The photograph is a close-up of the affected area · the affected area is the arm · the contributor is female: 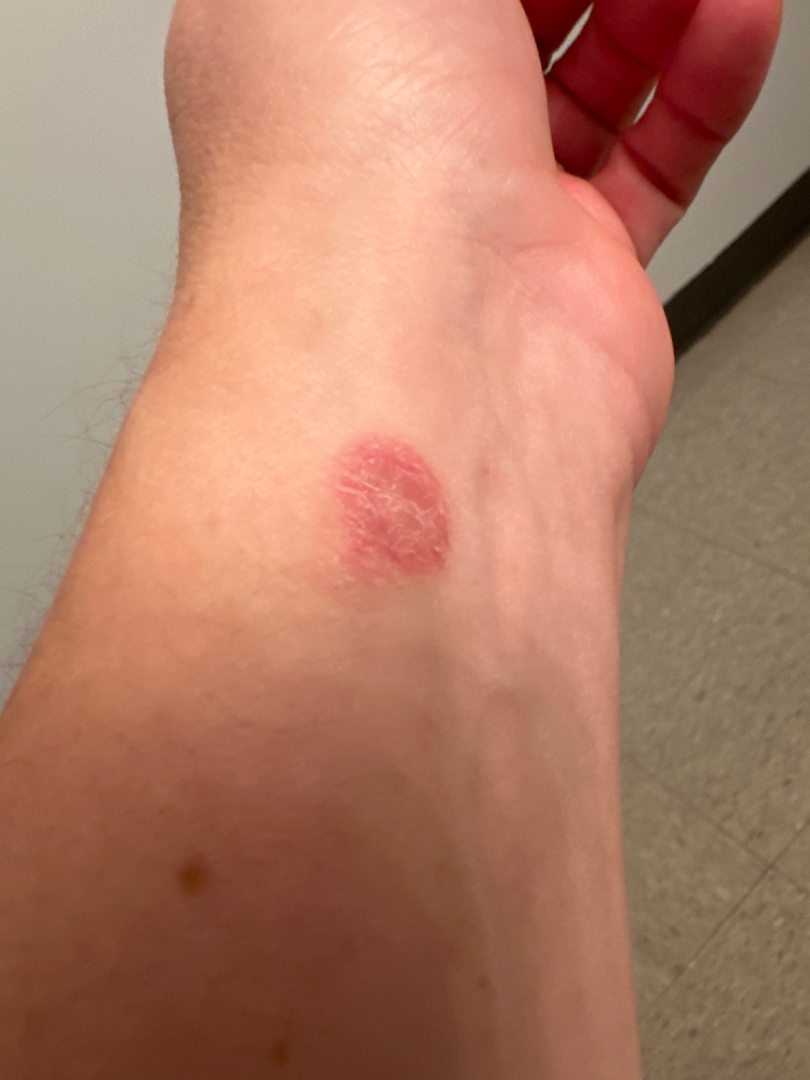Clinical context:
Reported duration is one to four weeks. The lesion is described as flat and rough or flaky.
Assessment:
On dermatologist assessment of the image, Allergic Contact Dermatitis (leading); Irritant Contact Dermatitis (possible).